The patient says their skin tans without first burning; the patient describes having numerous moles; dermoscopy of a skin lesion; a female subject 78 years old; collected as part of a research study, without a referral diagnosis; on a questionnaire the patient reported no immunosuppression.
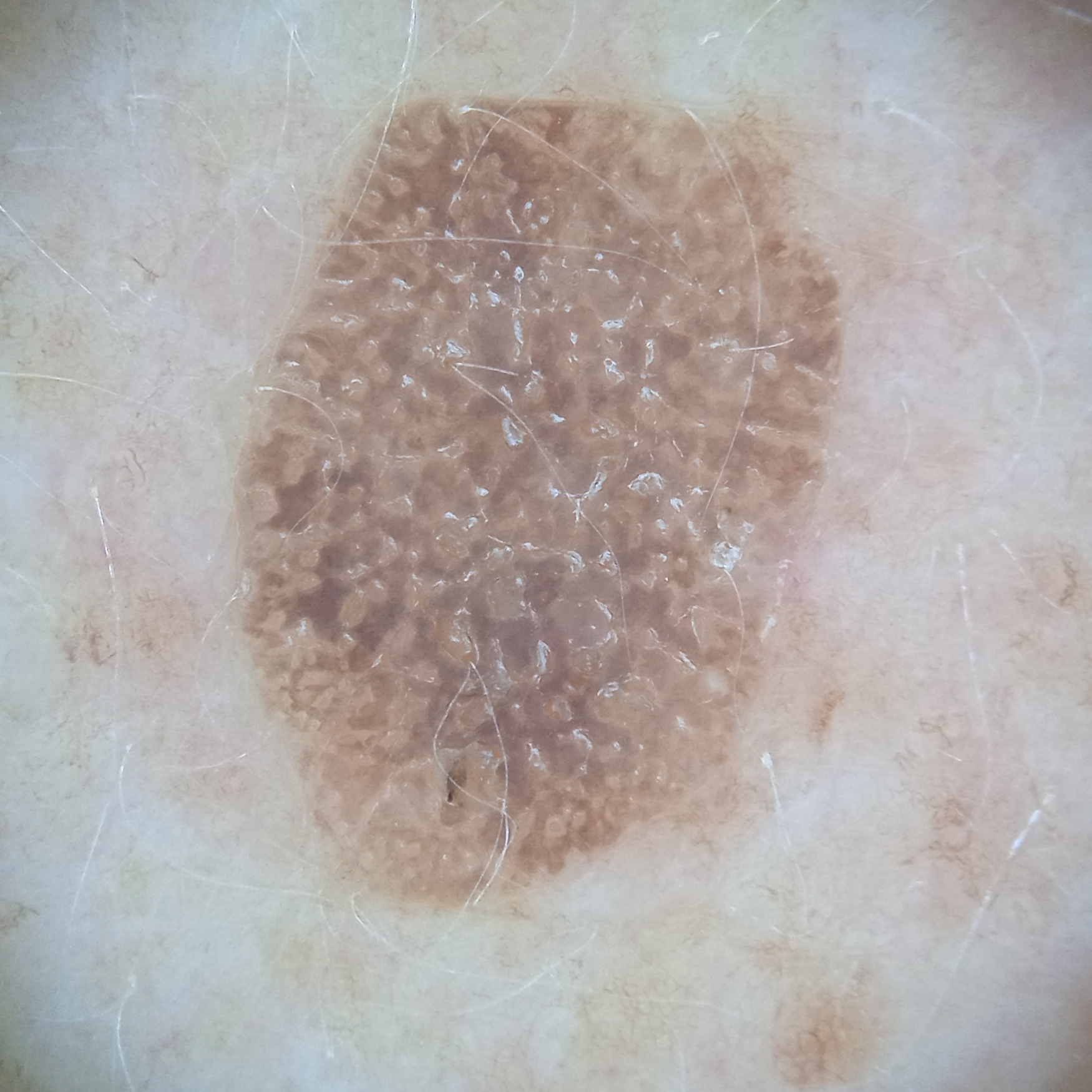Summary: The lesion is located on the back. The lesion measures approximately 9.6 mm. Assessment: On independent review by four dermatologists, the agreed diagnosis was a seborrheic keratosis; the reviewers were highly confident.